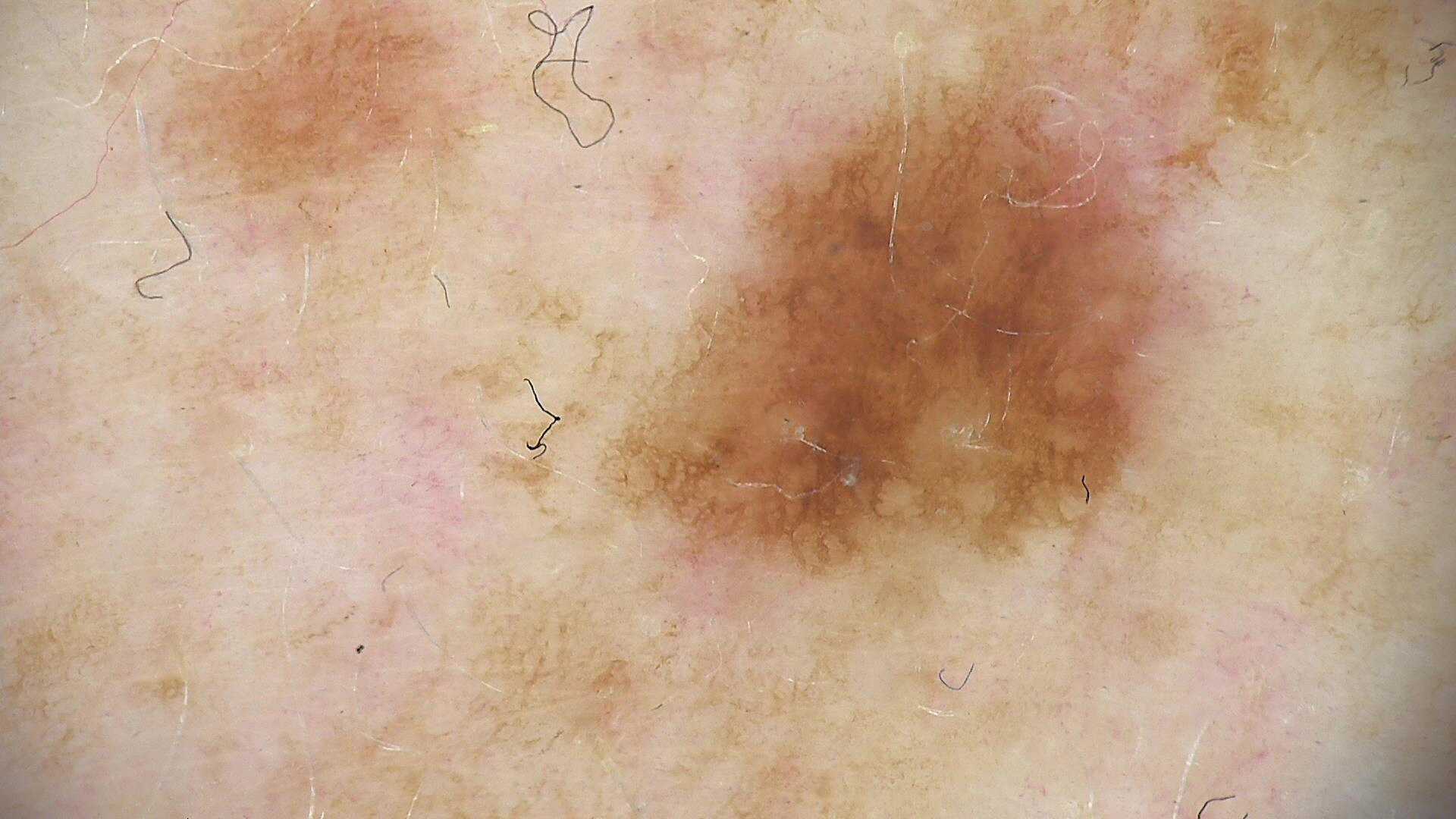class=dysplastic junctional nevus (expert consensus)